A dermoscopic image of a skin lesion: 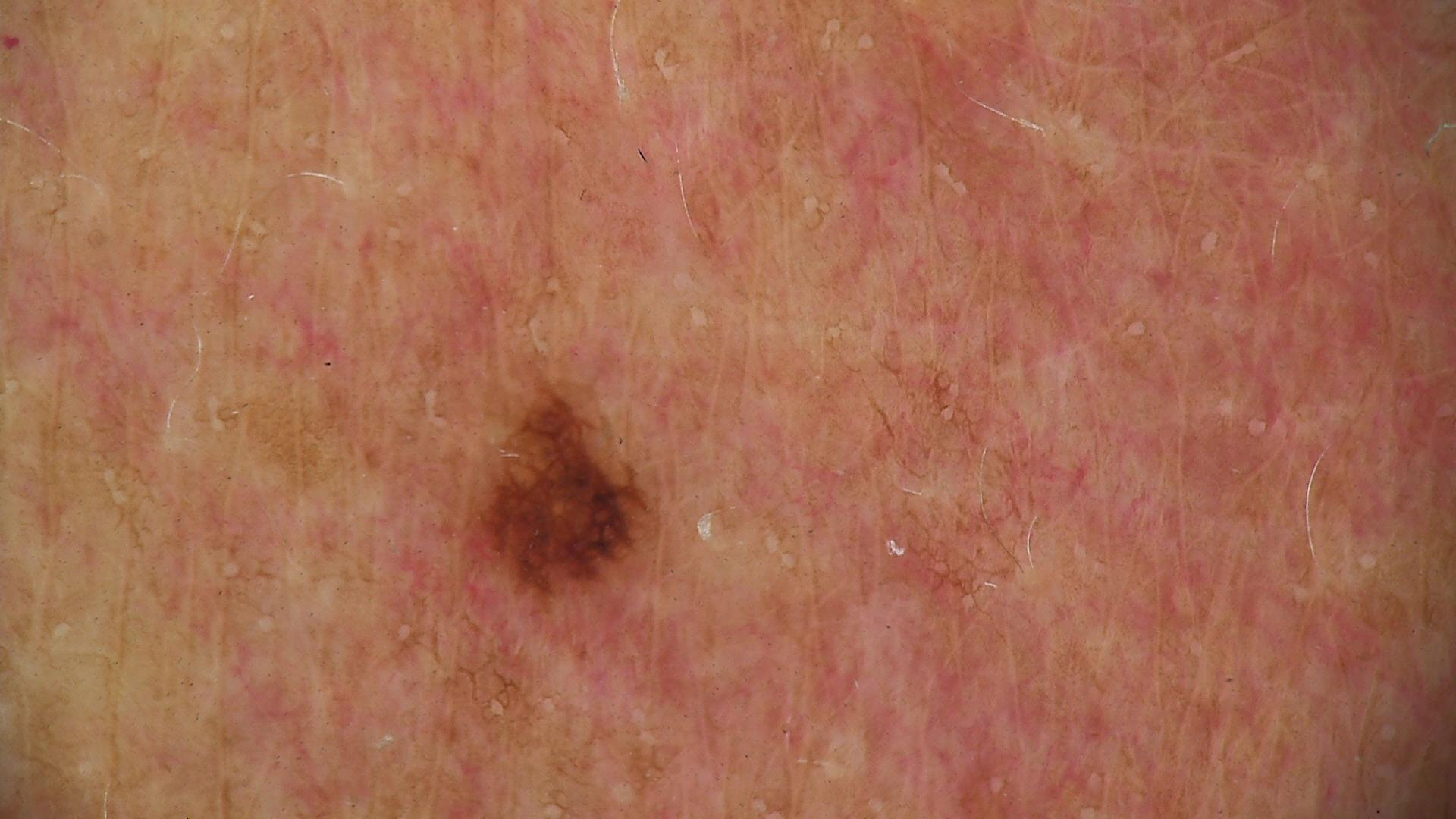Diagnosed as a dysplastic junctional nevus.